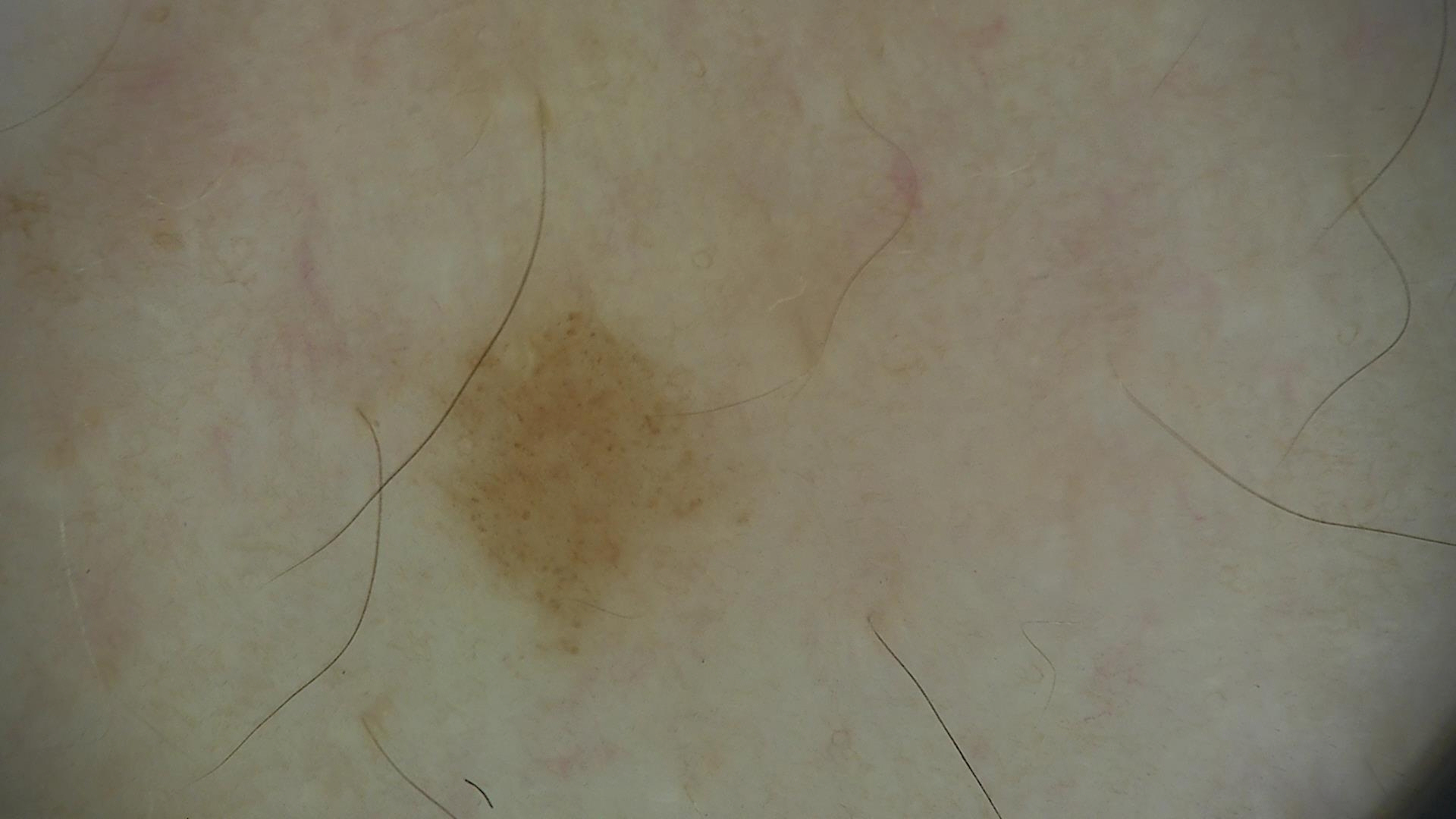A dermoscopy image of a single skin lesion. The diagnostic label was a benign lesion — a dysplastic junctional nevus.